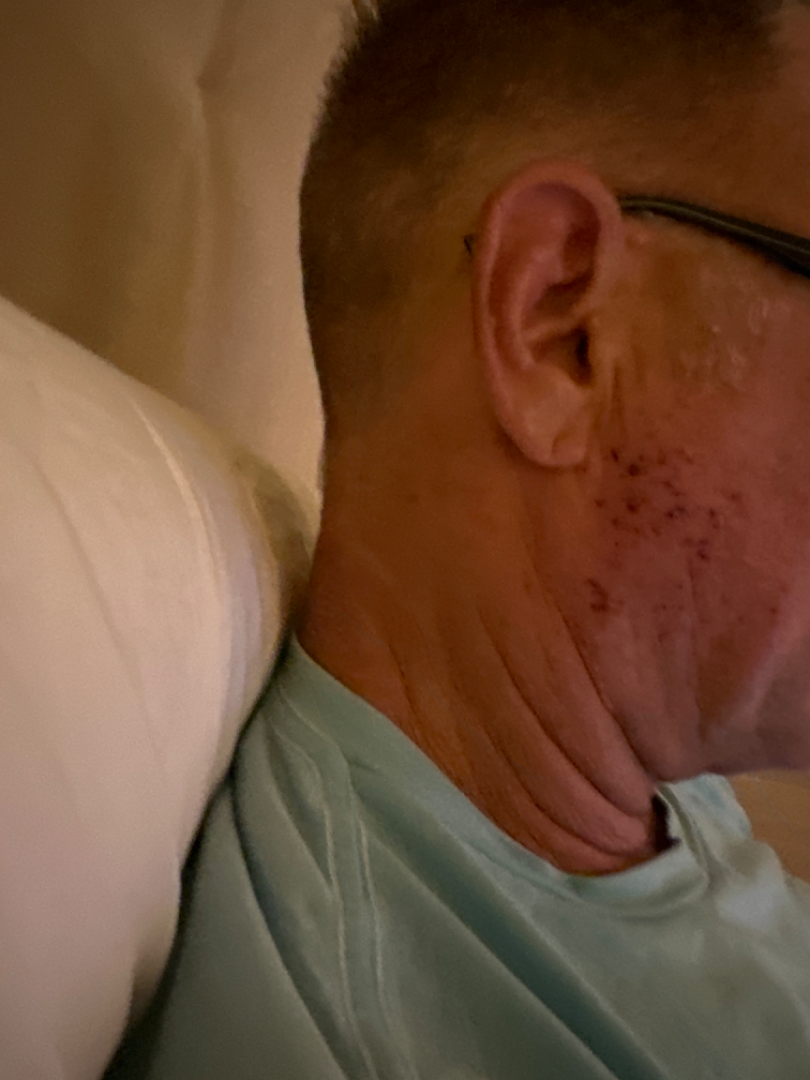The case was difficult to assess from the available photograph. The photo was captured at a distance. The head or neck is involved. The contributor reports bleeding, itching and burning.